An image taken at an angle. The lesion involves the top or side of the foot and leg. The condition has been present for one to three months. The patient described the issue as a pigmentary problem. Female subject, age 18–29. Symptoms reported: enlargement and bothersome appearance: 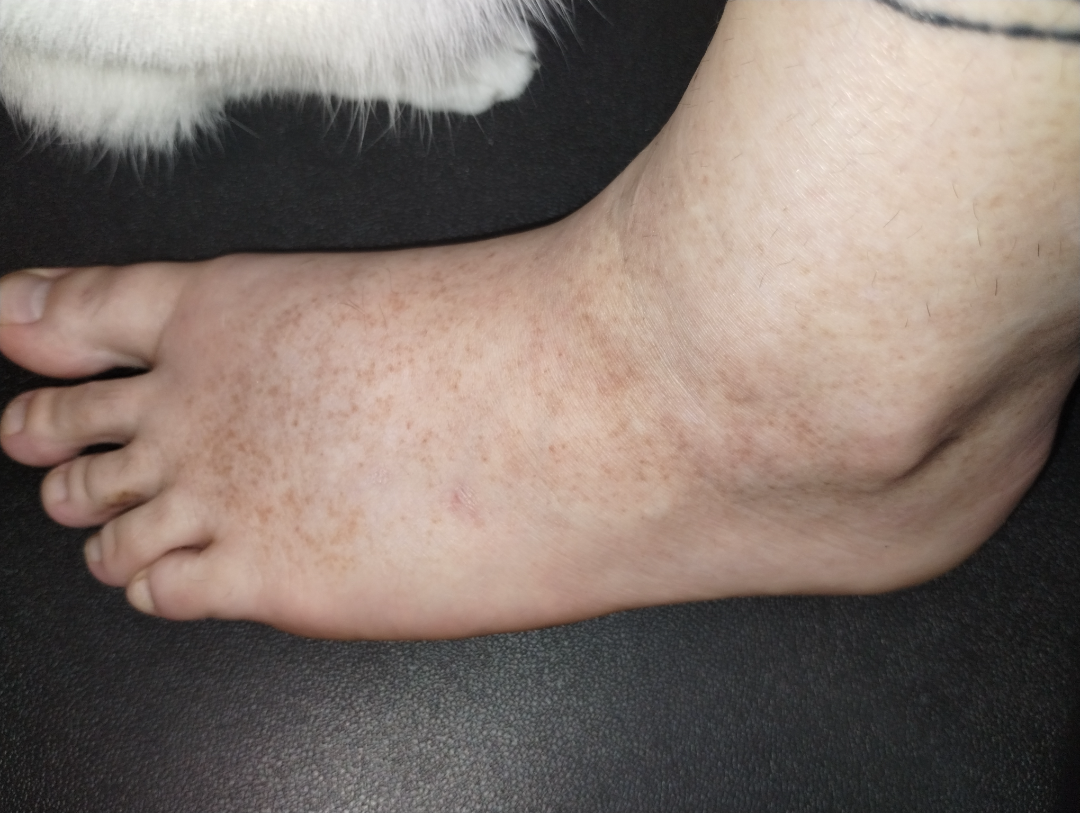Q: What conditions are considered?
A: favoring Hemosiderin pigmentation of lower limb due to varicose veins of lower limb; possibly Pigmented purpuric eruption